This is a close-up image · female patient, age 30–39:
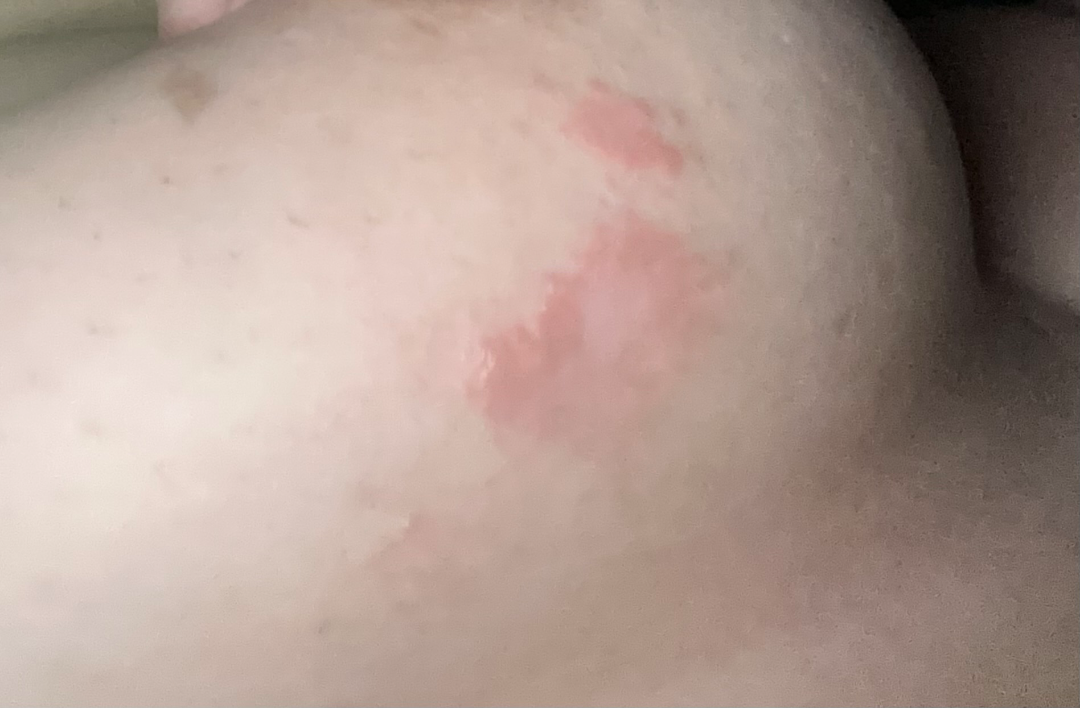Findings:
• assessment · indeterminate from the photograph